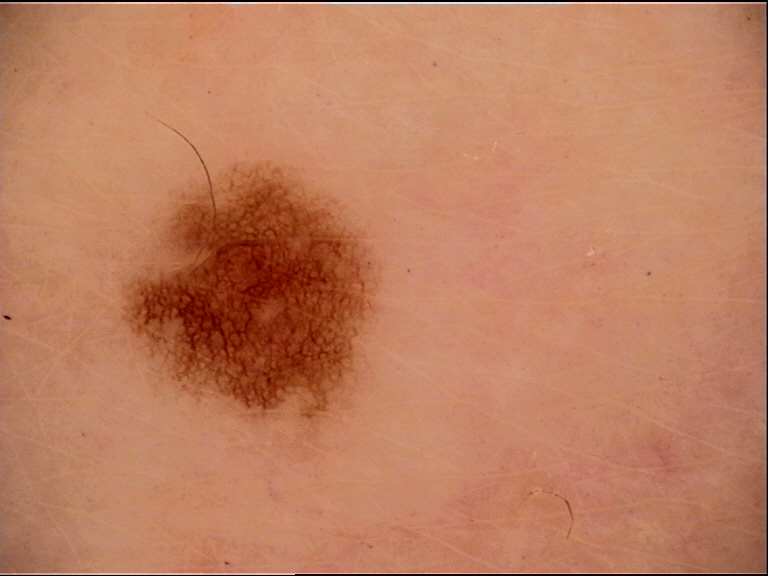Impression: Consistent with a junctional nevus.